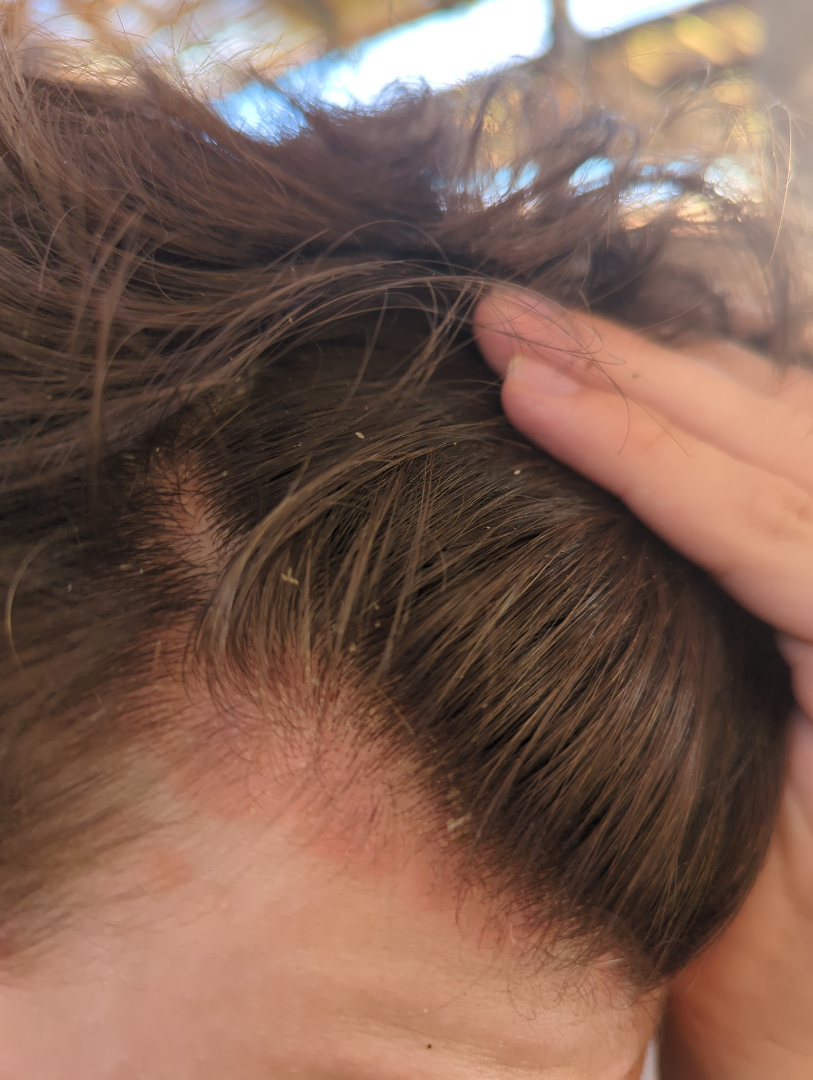No associated lesion symptoms were reported. Reported duration is three to twelve months. The head or neck is involved. This is a close-up image. Male patient, age 18–29. On dermatologist assessment of the image, the differential includes Psoriasis and Seborrheic Dermatitis, with no clear leading consideration.